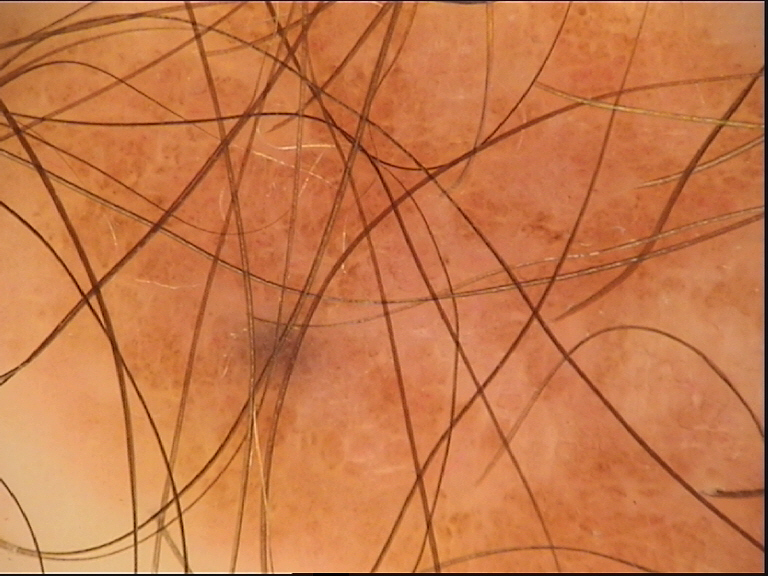Q: What was the diagnostic impression?
A: dysplastic compound nevus (expert consensus)